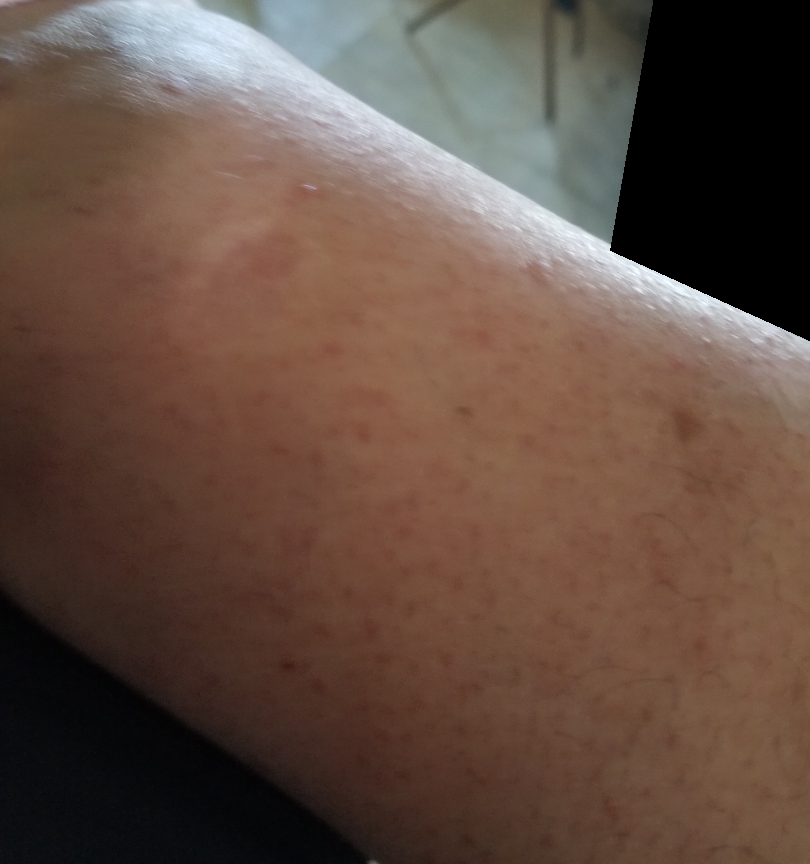The photo was captured at an angle. On remote dermatologist review, the impression was split between Stasis Dermatitis, Eczema and Allergic Contact Dermatitis.